Dermoscopy of a skin lesion. Acquired for a research image collection, with no referral diagnosis. A male patient aged 73:
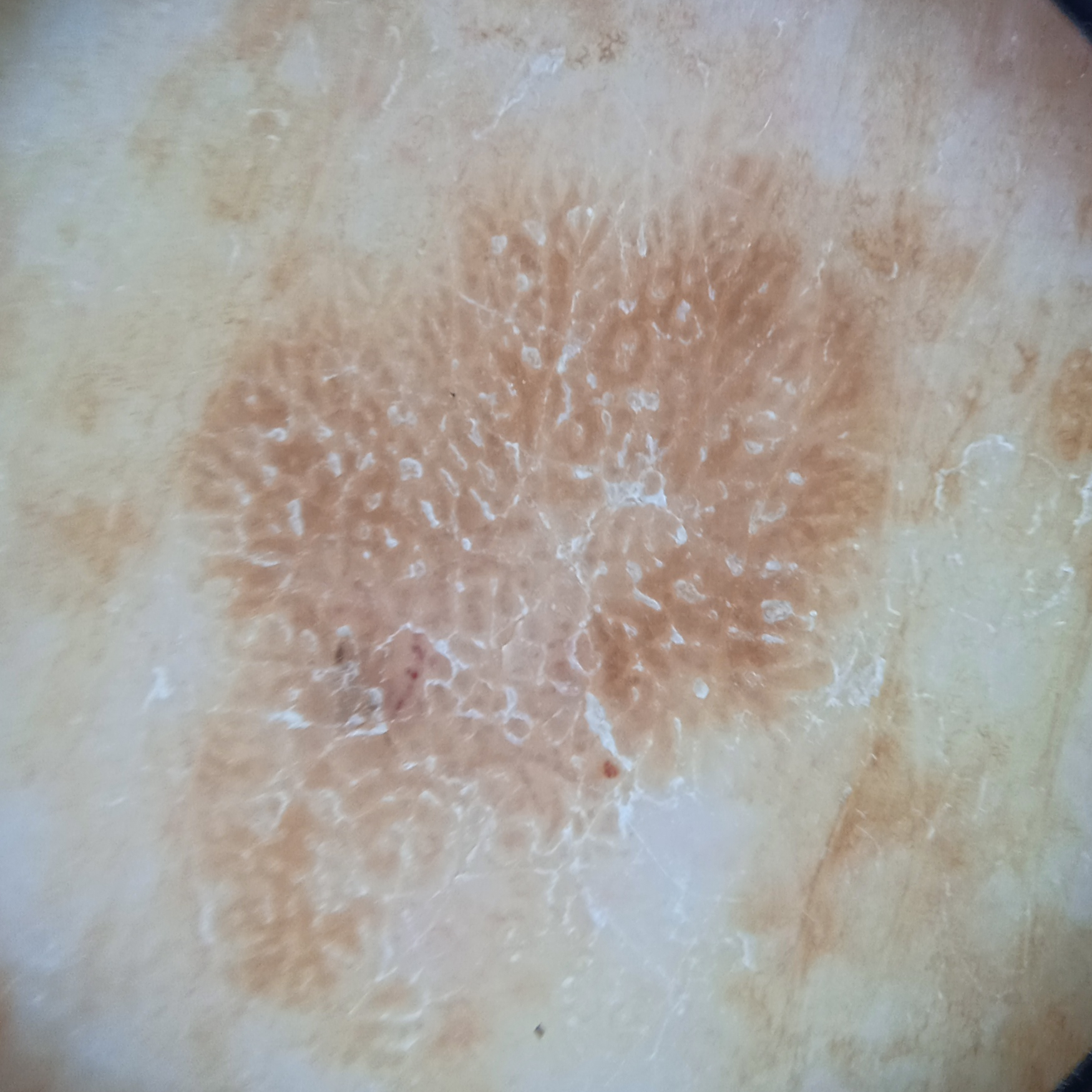* size: 10.7 mm
* diagnostic label: seborrheic keratosis (dermatologist consensus)